A male patient aged approximately 60 · a dermoscopic close-up of a skin lesion.
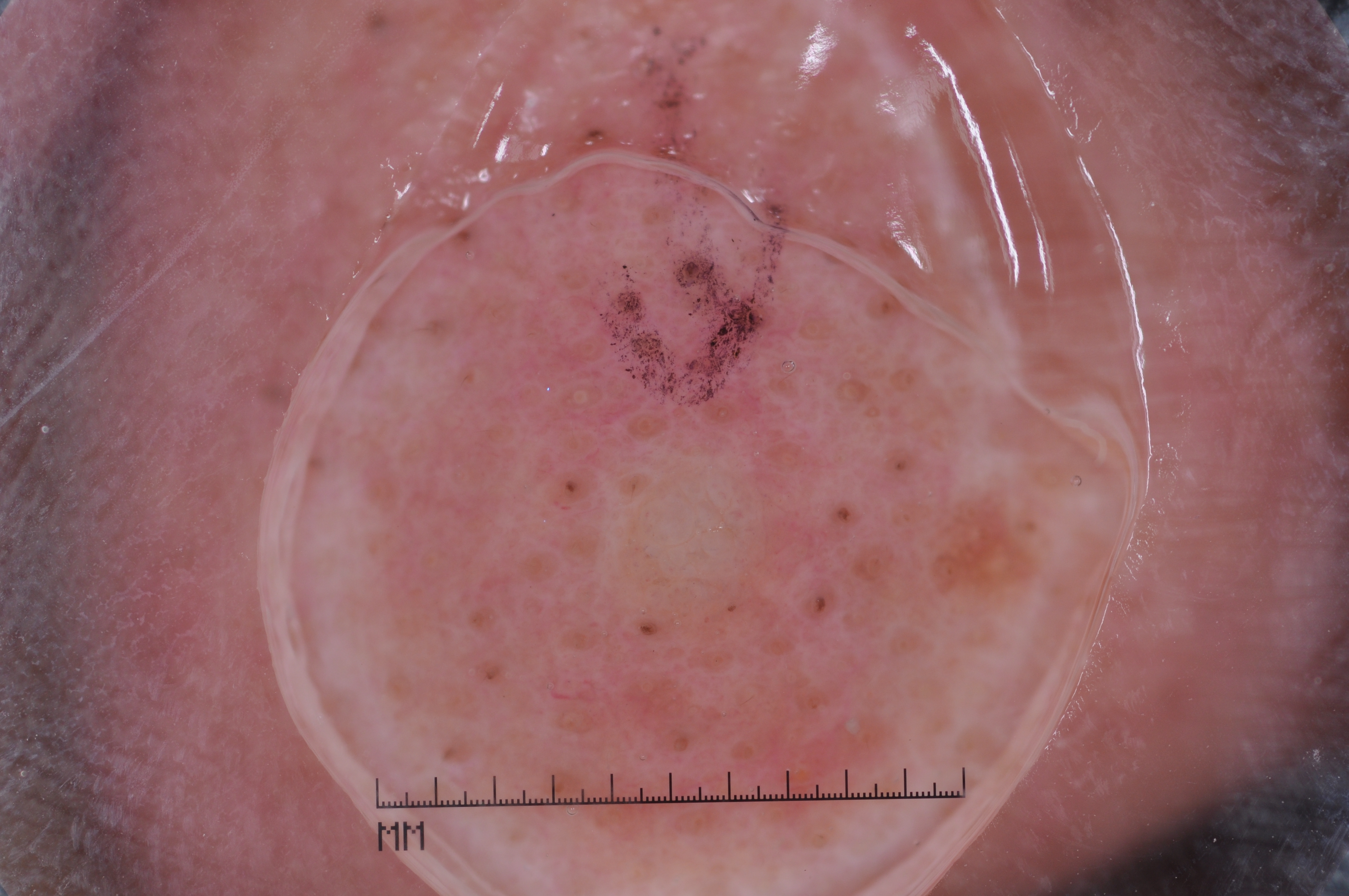lesion location = 345 226 1053 848
absent dermoscopic features = pigment network, streaks, milia-like cysts, and negative network
diagnostic label = a seborrheic keratosis, a benign lesion